The photograph was taken at an angle, located on the leg.
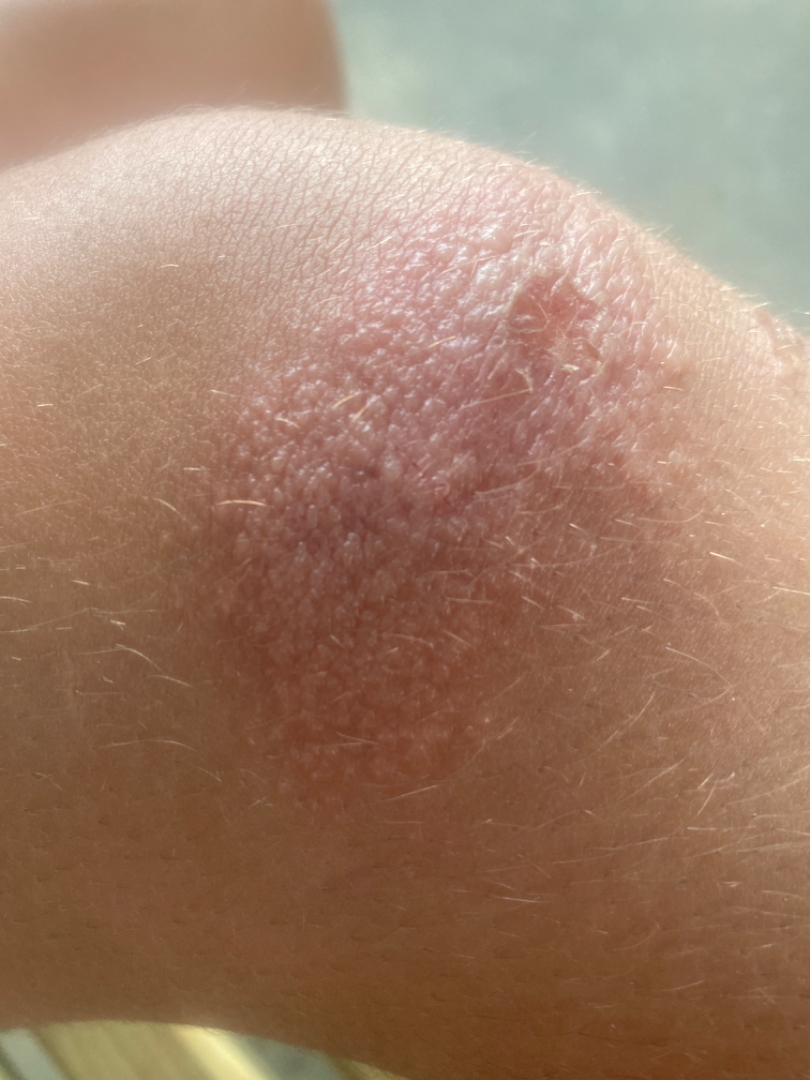Findings: The case was indeterminate on photographic review. Background: Fitzpatrick phototype IV. The lesion is associated with itching. Present for less than one week. The patient considered this a rash. Texture is reported as raised or bumpy.